The contributor is 30–39, male; a close-up photograph; located on the front of the torso.
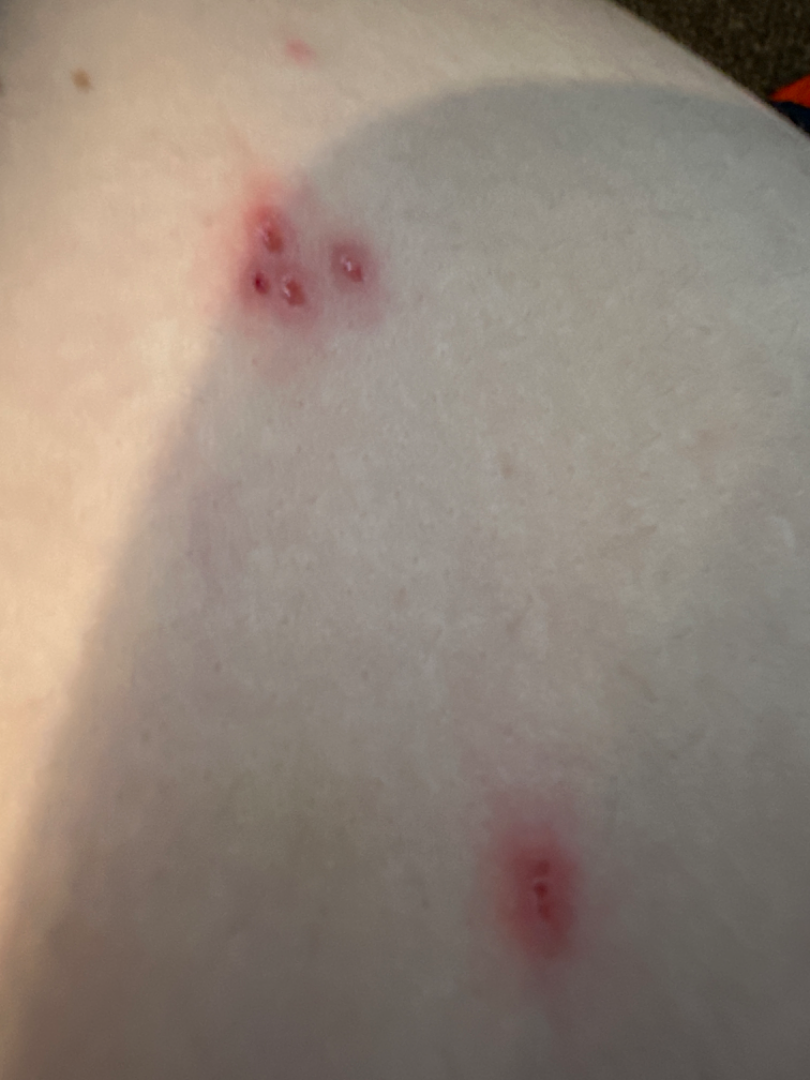| key | value |
|---|---|
| assessment | not assessable |